A dermoscopic close-up of a skin lesion:
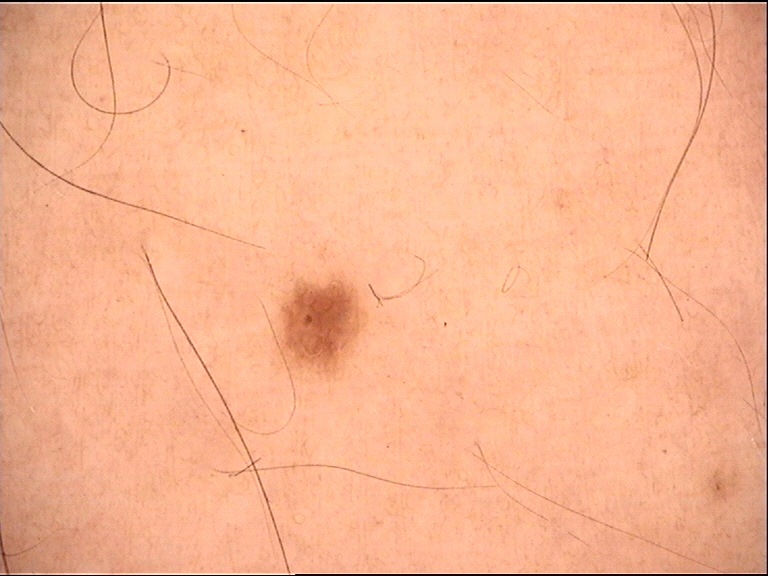| feature | finding |
|---|---|
| diagnostic label | dysplastic junctional nevus (expert consensus) |